A male subject roughly 15 years of age, dermoscopy of a skin lesion:
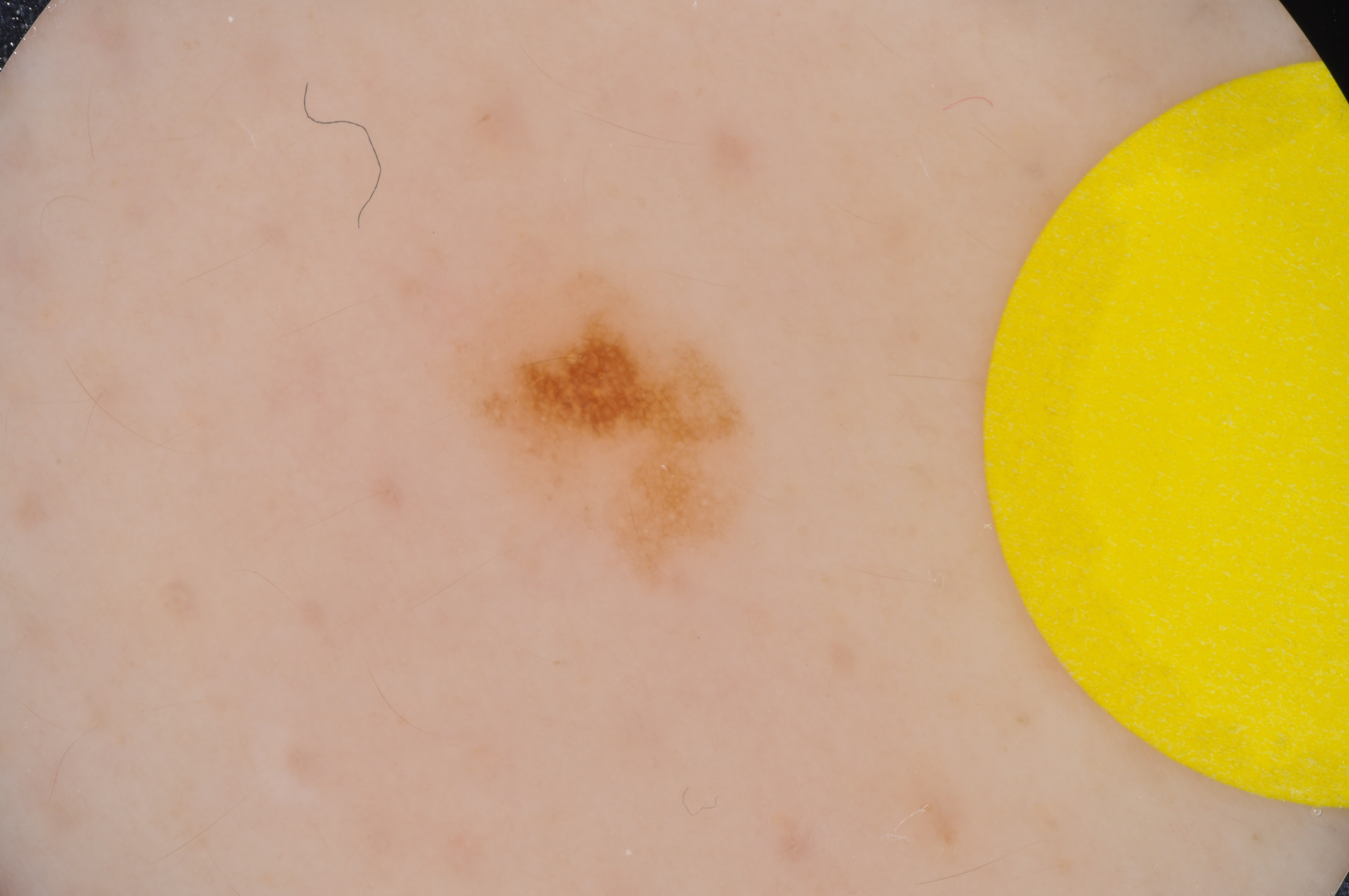A small lesion within a wider field of skin. In (x1, y1, x2, y2) order, the lesion occupies the region 447 262 779 592. Dermoscopic assessment notes milia-like cysts and pigment network. The lesion was assessed as a melanocytic nevus, a benign lesion.